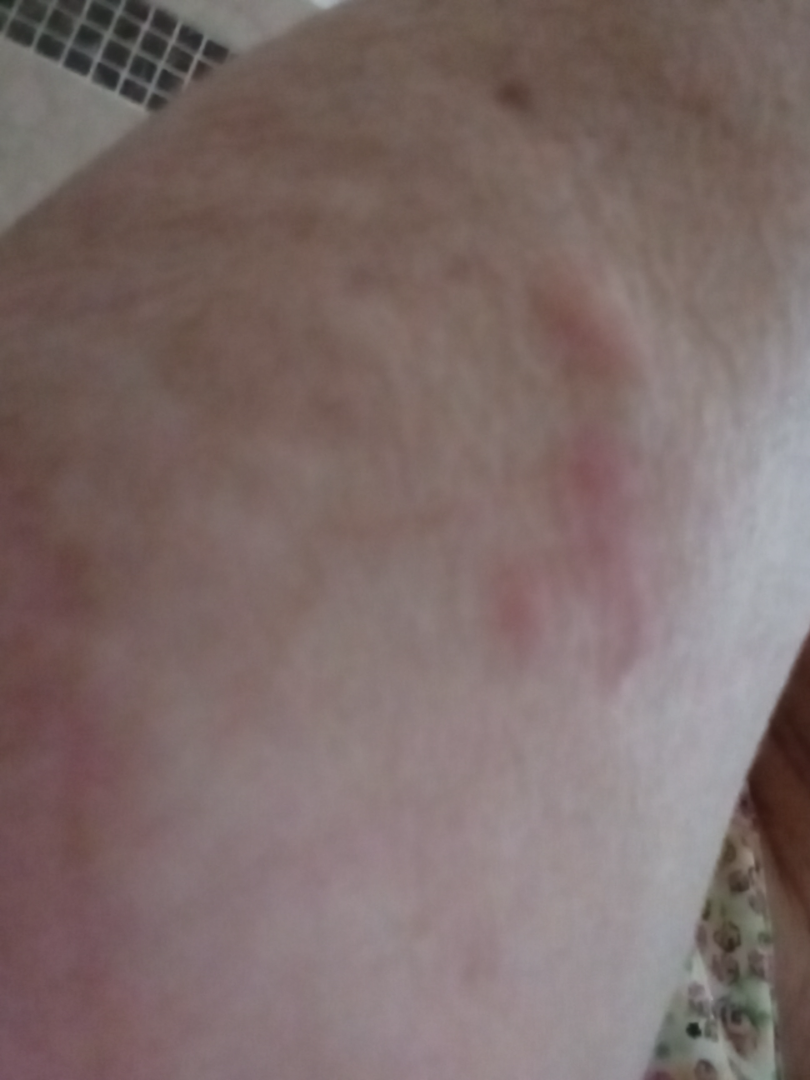The skin findings could not be characterized from the image. The photograph is a close-up of the affected area. The lesion involves the arm. Present for less than one week. Lay graders estimated 2 on the Monk skin tone scale. Texture is reported as flat. No constitutional symptoms were reported. The patient reports itching.